The photo was captured at an angle.
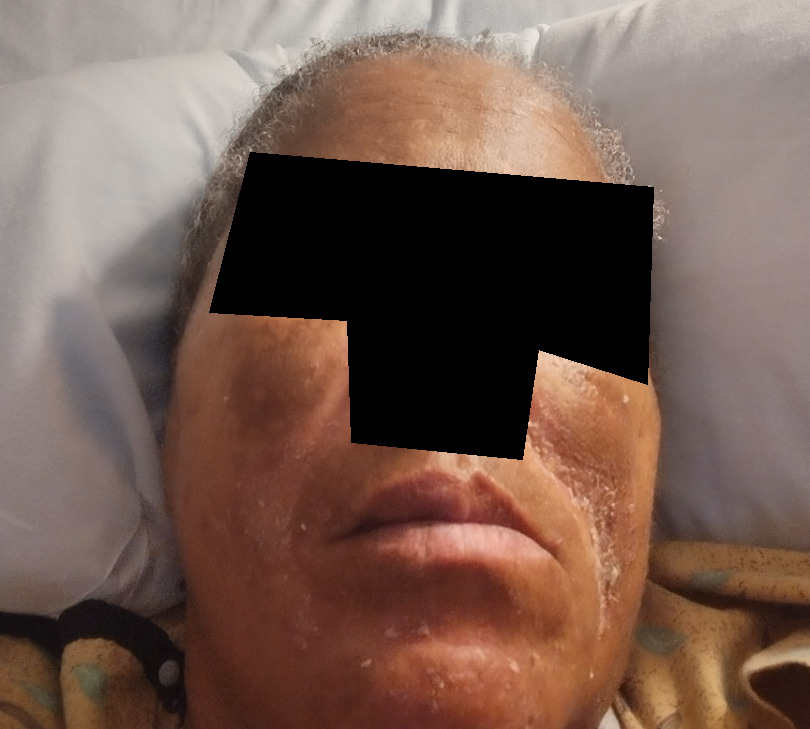The case was indeterminate on photographic review.